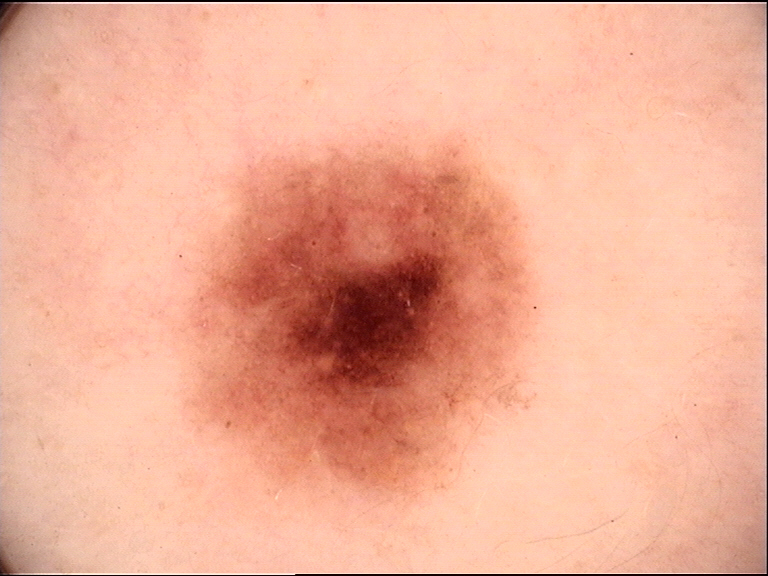{
  "image": "dermoscopy",
  "diagnosis": {
    "name": "dysplastic junctional nevus",
    "code": "jd",
    "malignancy": "benign",
    "super_class": "melanocytic",
    "confirmation": "expert consensus"
  }
}